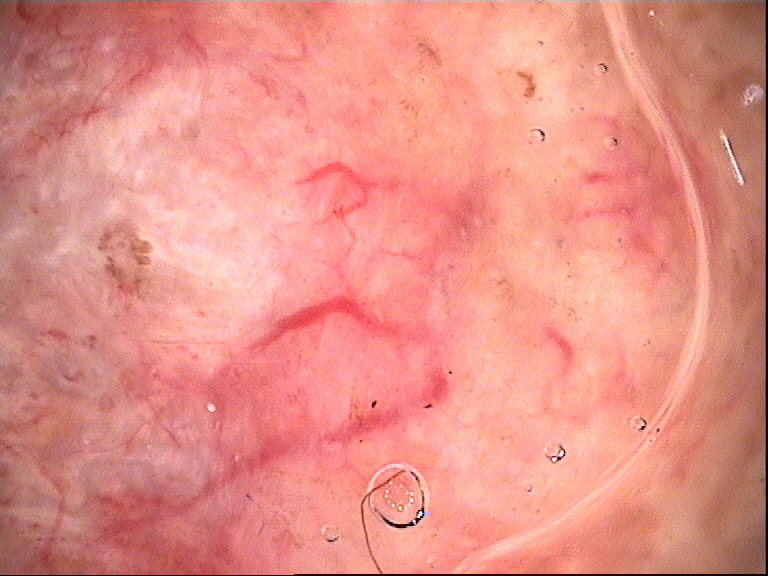A dermoscopic close-up of a skin lesion.
Biopsy-confirmed as a malignant, keratinocytic lesion — a basal cell carcinoma.